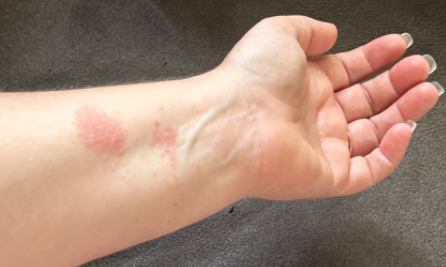On dermatologist assessment of the image, most consistent with Allergic Contact Dermatitis.